A patient 44 years of age. A clinical close-up photograph of a skin lesion — 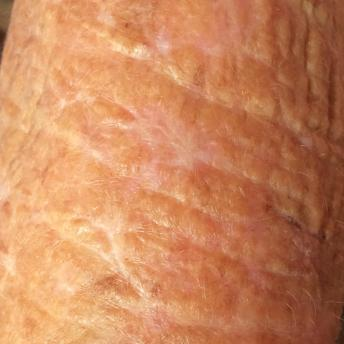Clinical context:
The lesion involves a forearm. The patient reports that the lesion itches, but has not changed and is not elevated.
Impression:
Consistent with an actinic keratosis.